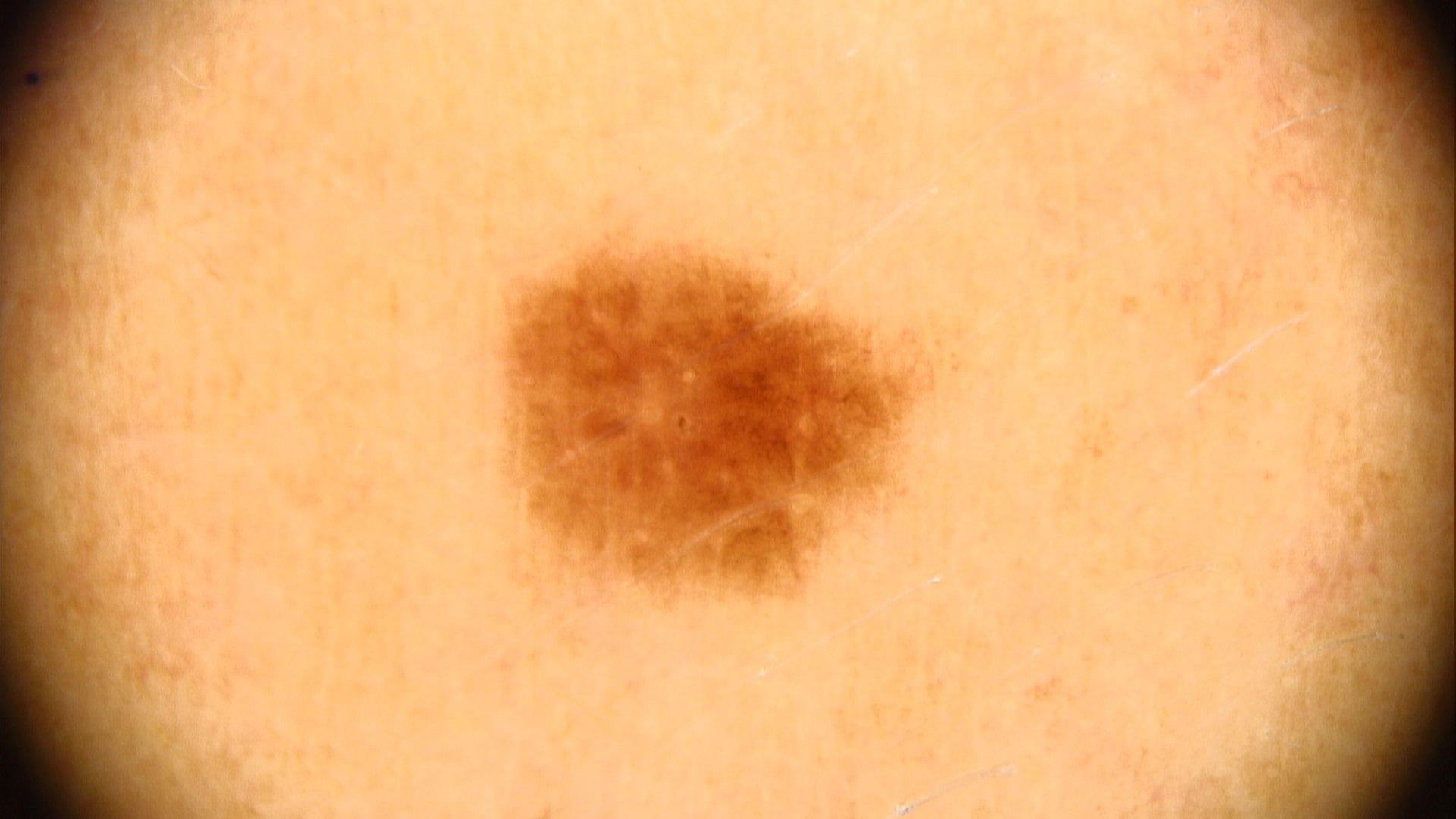{
  "melanoma_history": {
    "personal_hx_melanoma": false,
    "family_hx_melanoma": true
  },
  "skin_type": "III",
  "diagnosis": {
    "name": "Nevus",
    "malignancy": "benign",
    "confirmation": "expert clinical impression",
    "lineage": "melanocytic"
  }
}